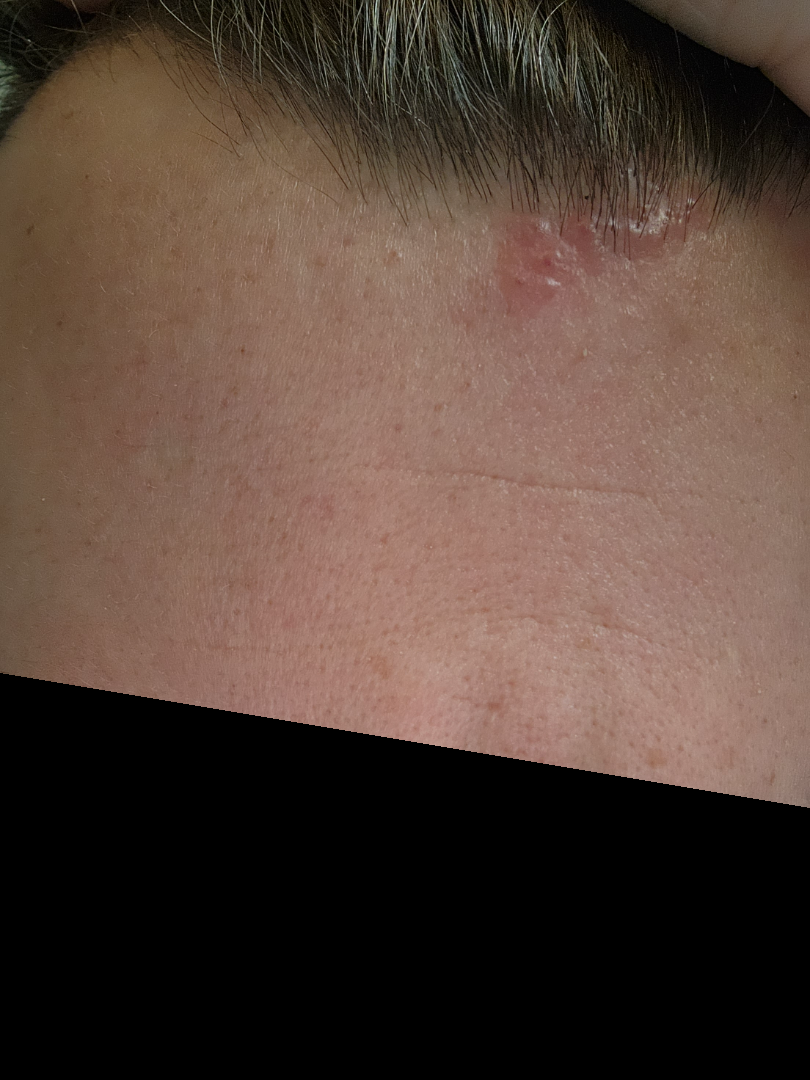Review: The case was indeterminate on photographic review.